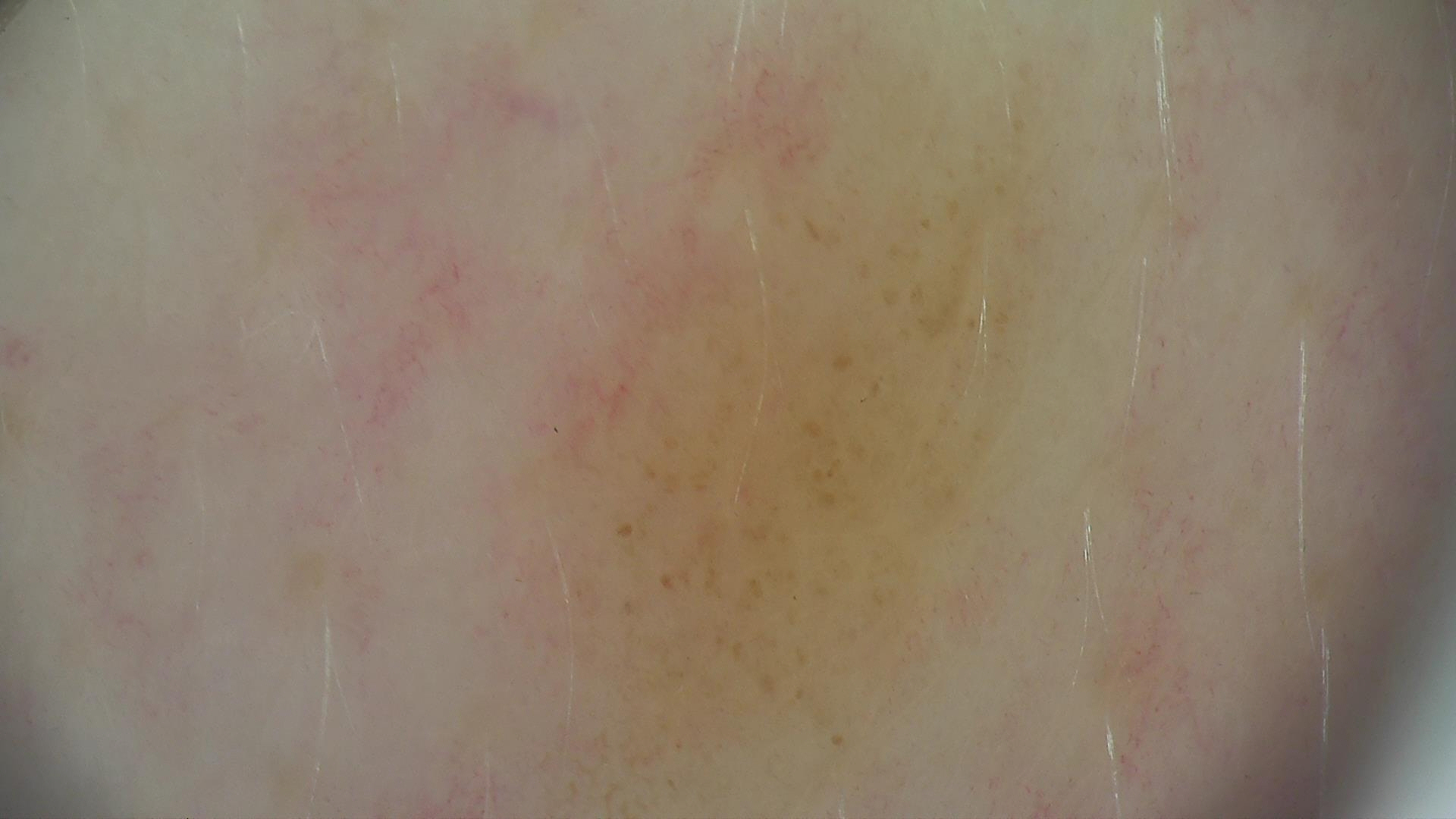A skin lesion imaged with a dermatoscope.
This is a banal lesion.
The diagnostic label was a dermal nevus.